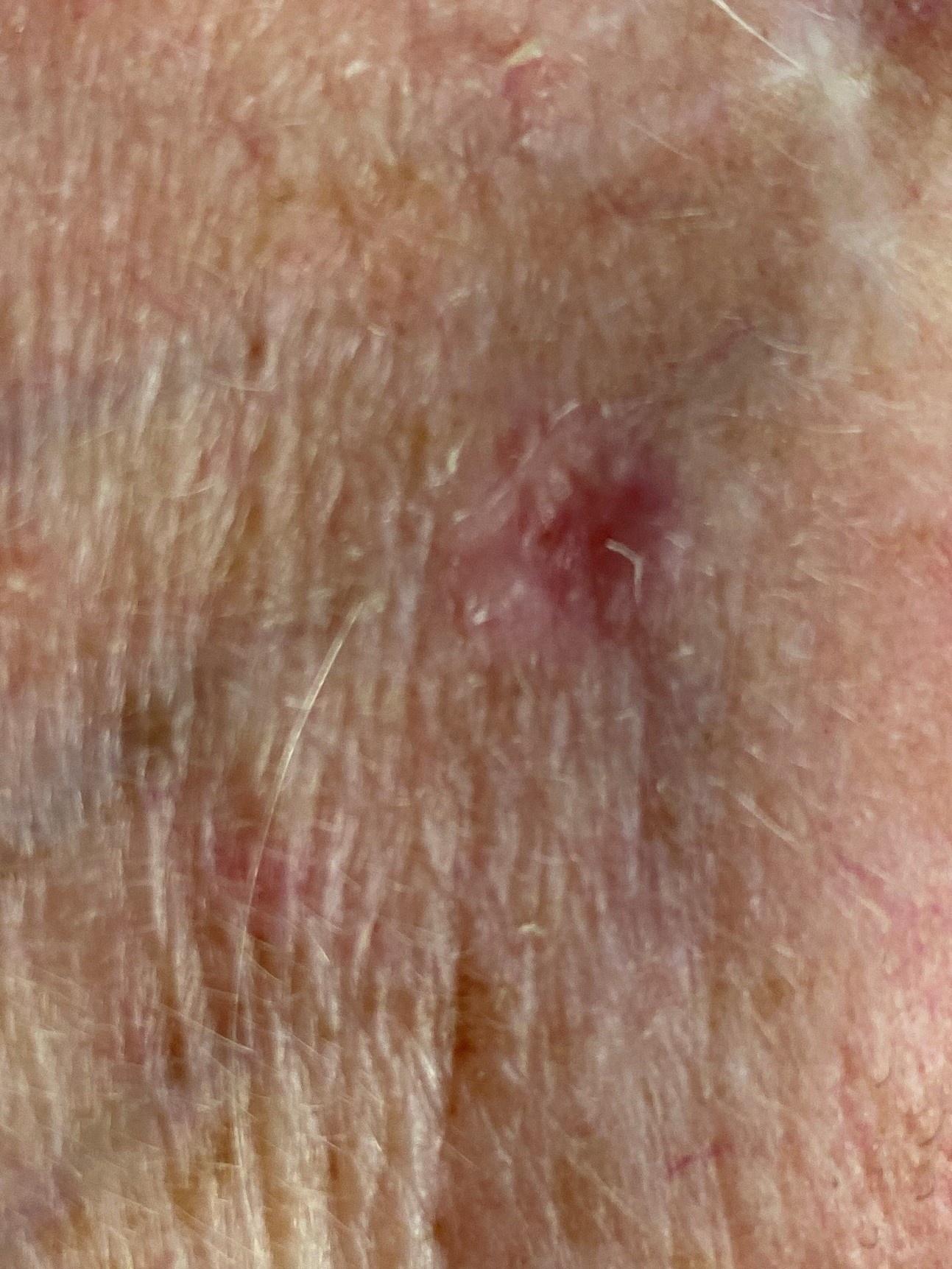A female subject in their mid-80s or older.
A clinical overview photograph of a skin lesion.
Located on the head or neck.
Histopathologically confirmed as a malignant lesion — a basal cell carcinoma.